An image taken at a distance · located on the leg: 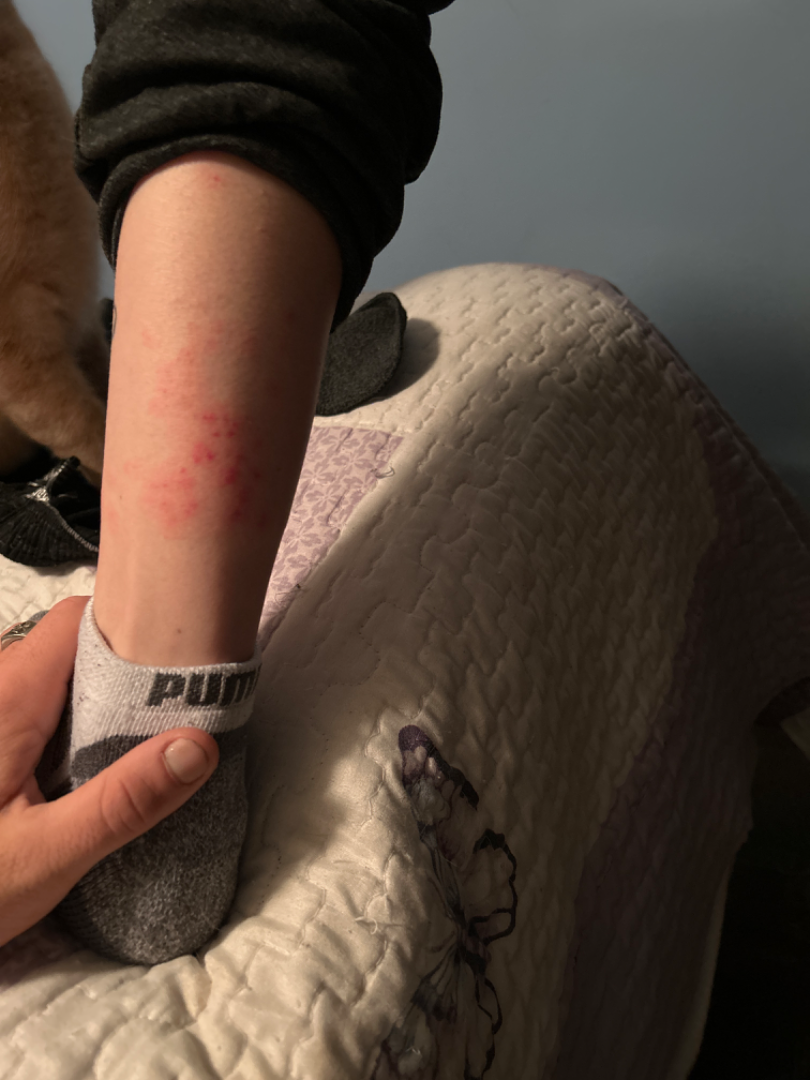differential diagnosis: Folliculitis (considered); Acute dermatitis, NOS (considered)